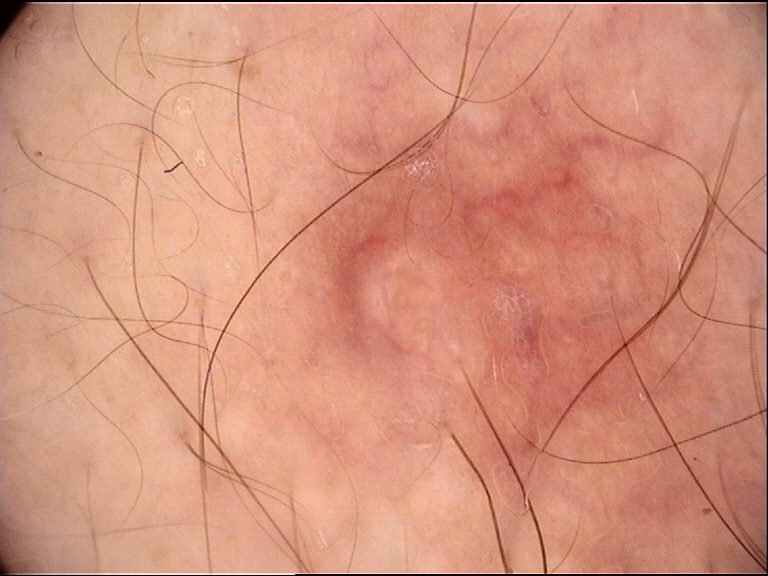diagnosis:
  name: dermal nevus
  code: db
  malignancy: benign
  super_class: melanocytic
  confirmation: expert consensus